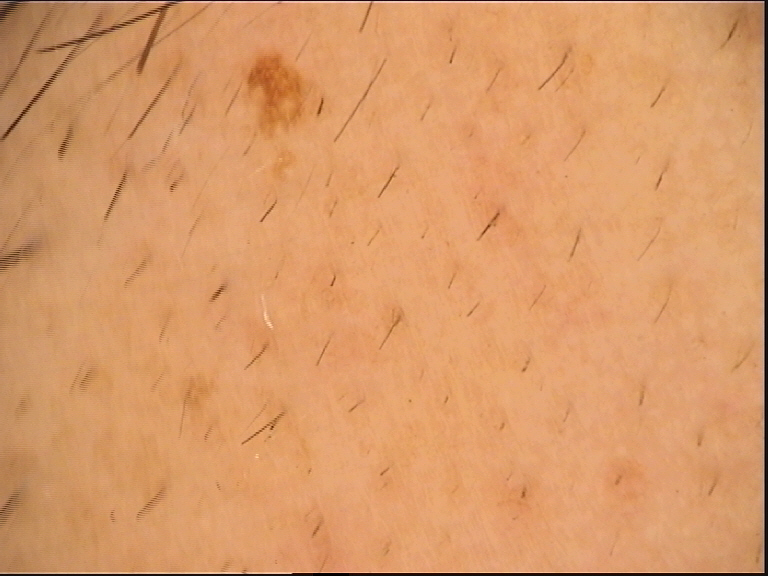Case:
• modality: dermatoscopy
• class: junctional nevus (expert consensus)